This image was taken at an angle; female subject, age 40–49: 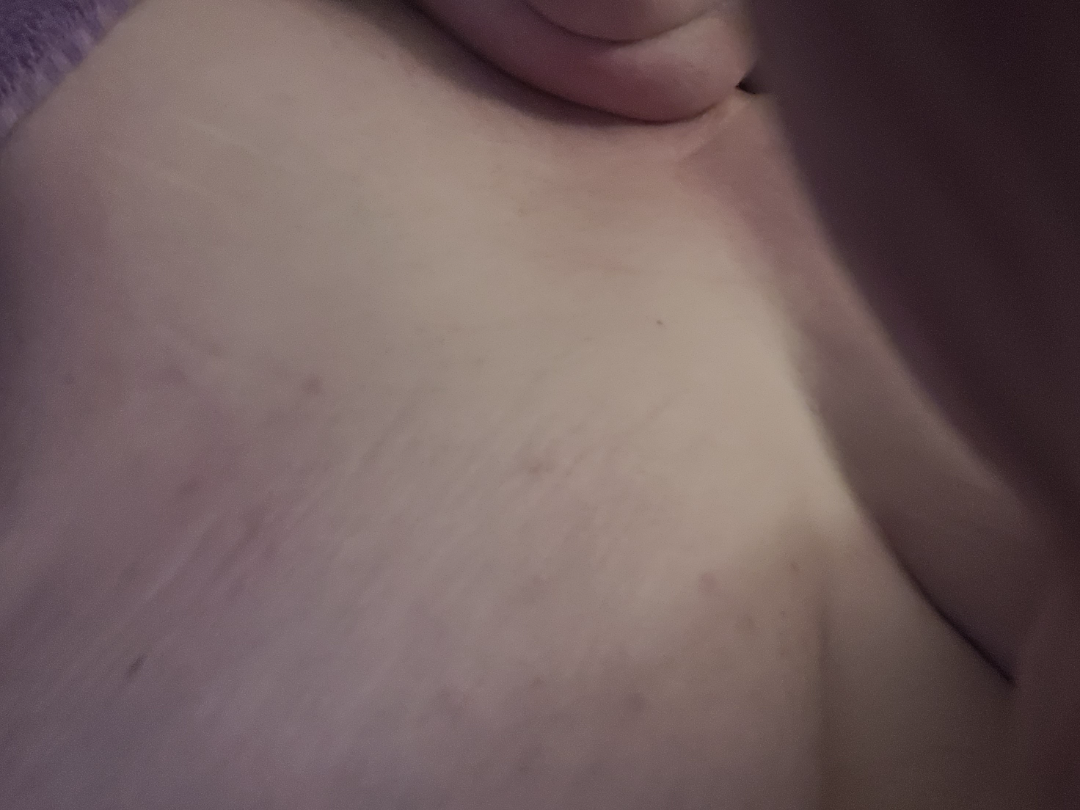Findings: The reviewer was unable to grade this case for skin condition.